A dermoscopic view of a skin lesion; a male patient roughly 85 years of age or older: 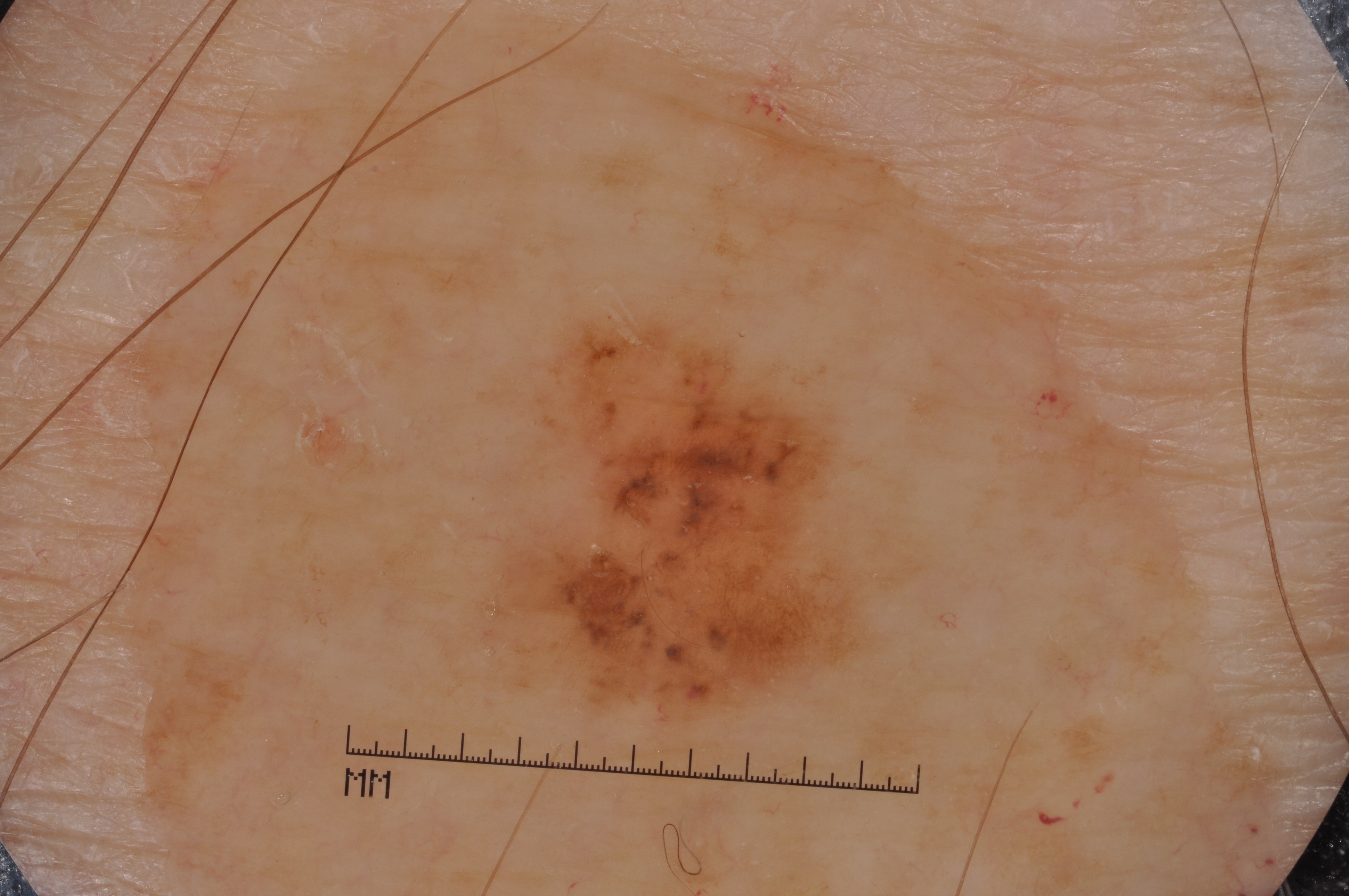features: pigment network and milia-like cysts | size: ~11% of the field | location: [436,270,932,777] | diagnostic label: a melanoma.